The photo was captured at an angle. The lesion involves the leg.
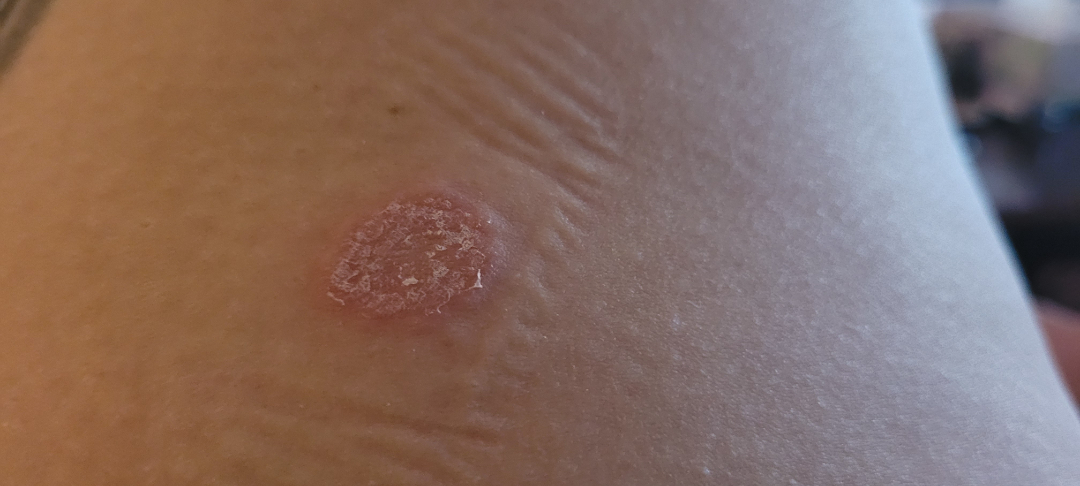assessment — ungradable on photographic review; lesion texture — raised or bumpy and rough or flaky; history — less than one week; associated systemic symptoms — none reported; symptoms — itching.